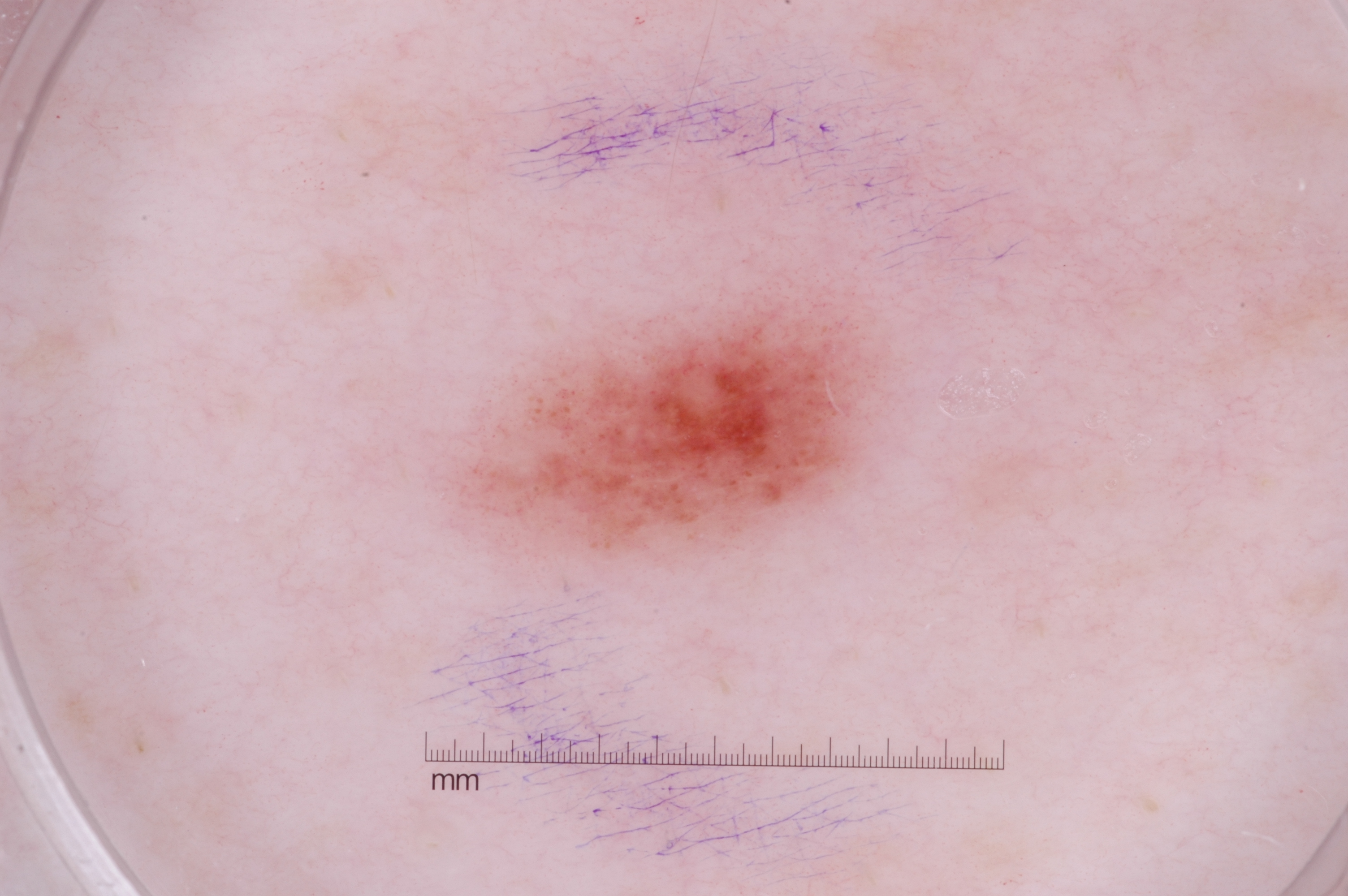Findings:
- modality: dermoscopic image
- lesion location: <box>453, 287, 885, 567</box>
- diagnostic label: a melanocytic nevus